The patient indicates the lesion is raised or bumpy; the photograph is a close-up of the affected area; the lesion is associated with bothersome appearance; the lesion involves the arm and leg — 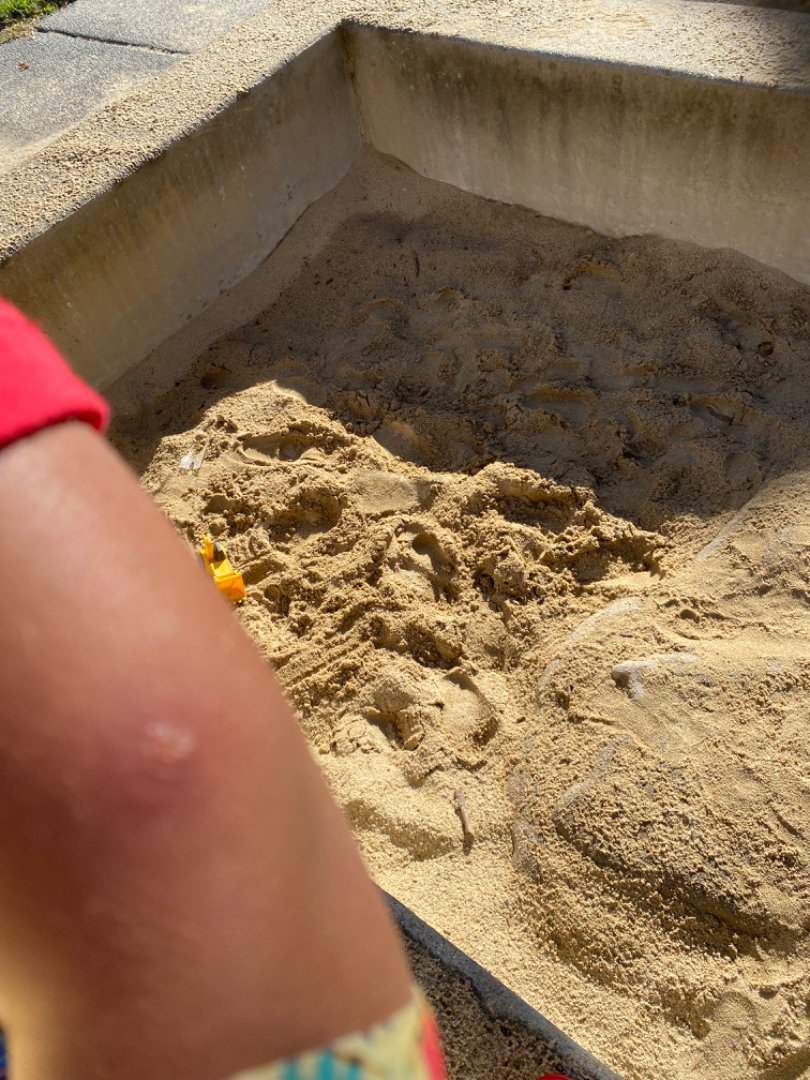assessment: could not be assessed.